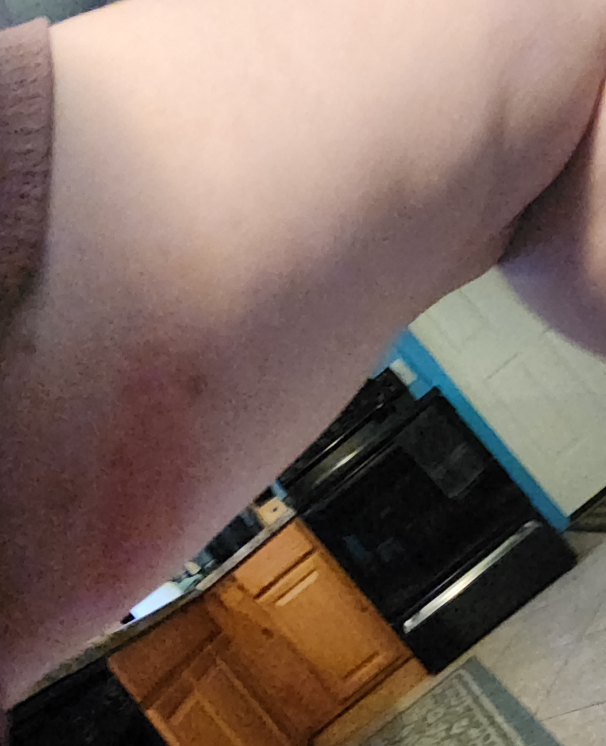Assessment:
Three dermatologists each reviewed the case: the leading consideration is Contact dermatitis; possibly Eczema; also on the differential is Allergic Contact Dermatitis.